Dermoscopy of a skin lesion.
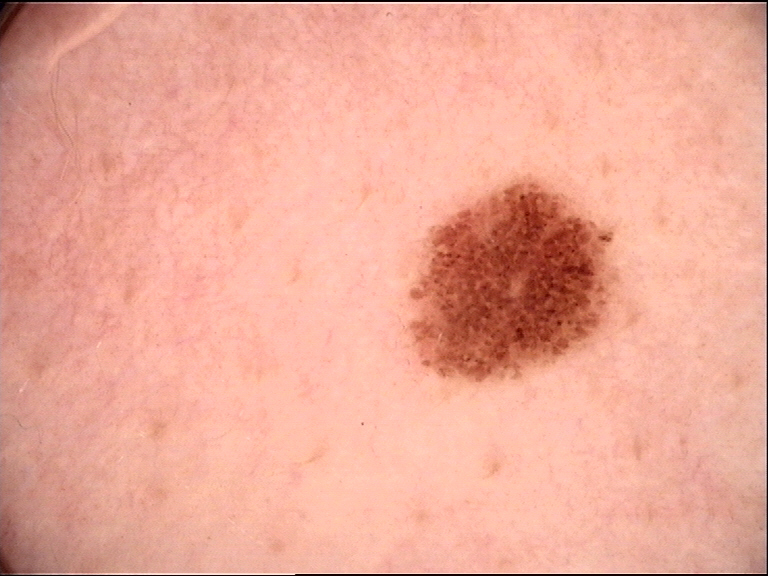Conclusion: The diagnosis was a banal lesion — a junctional nevus.